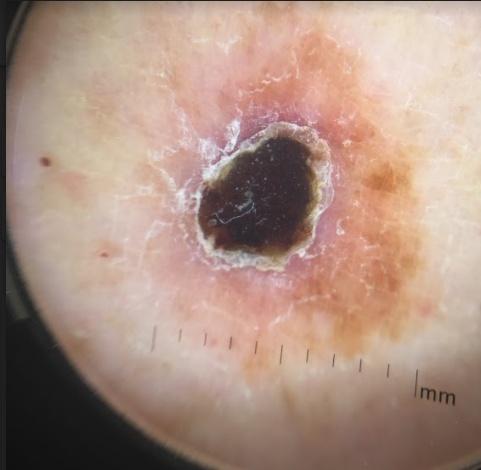<record>
  <image>dermoscopy</image>
  <patient>
    <age_approx>85+</age_approx>
    <sex>female</sex>
  </patient>
  <melanoma_history>
    <personal_hx_melanoma>true</personal_hx_melanoma>
  </melanoma_history>
  <skin_type>II</skin_type>
  <lesion_location>
    <region>a lower extremity</region>
  </lesion_location>
  <diagnosis>
    <name>Melanoma</name>
    <malignancy>malignant</malignancy>
    <confirmation>histopathology</confirmation>
  </diagnosis>
</record>